A patient in their 40s; a clinical photograph of a skin lesion — 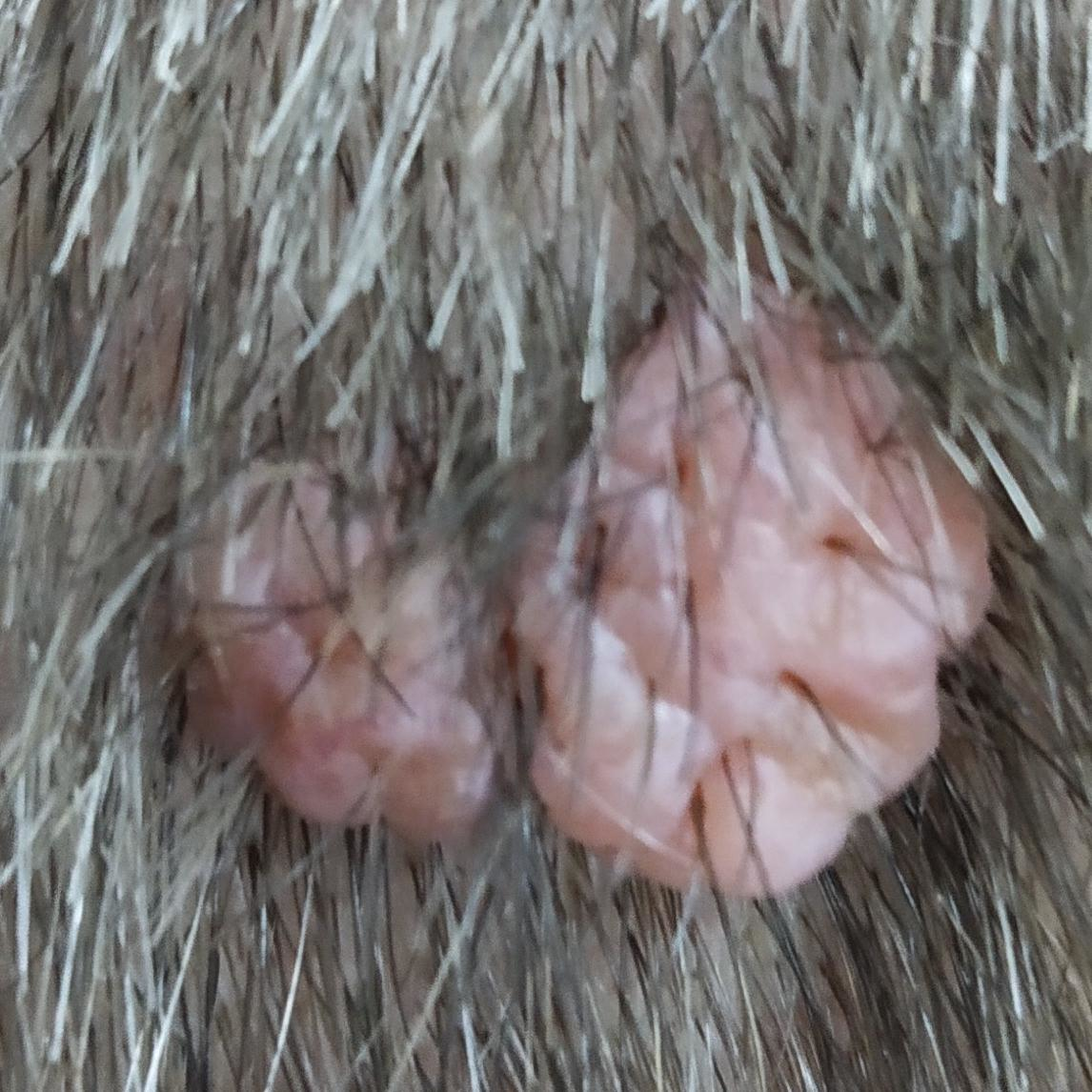Q: What is the anatomic site?
A: the scalp
Q: What was the clinical impression?
A: nevus (clinical consensus)